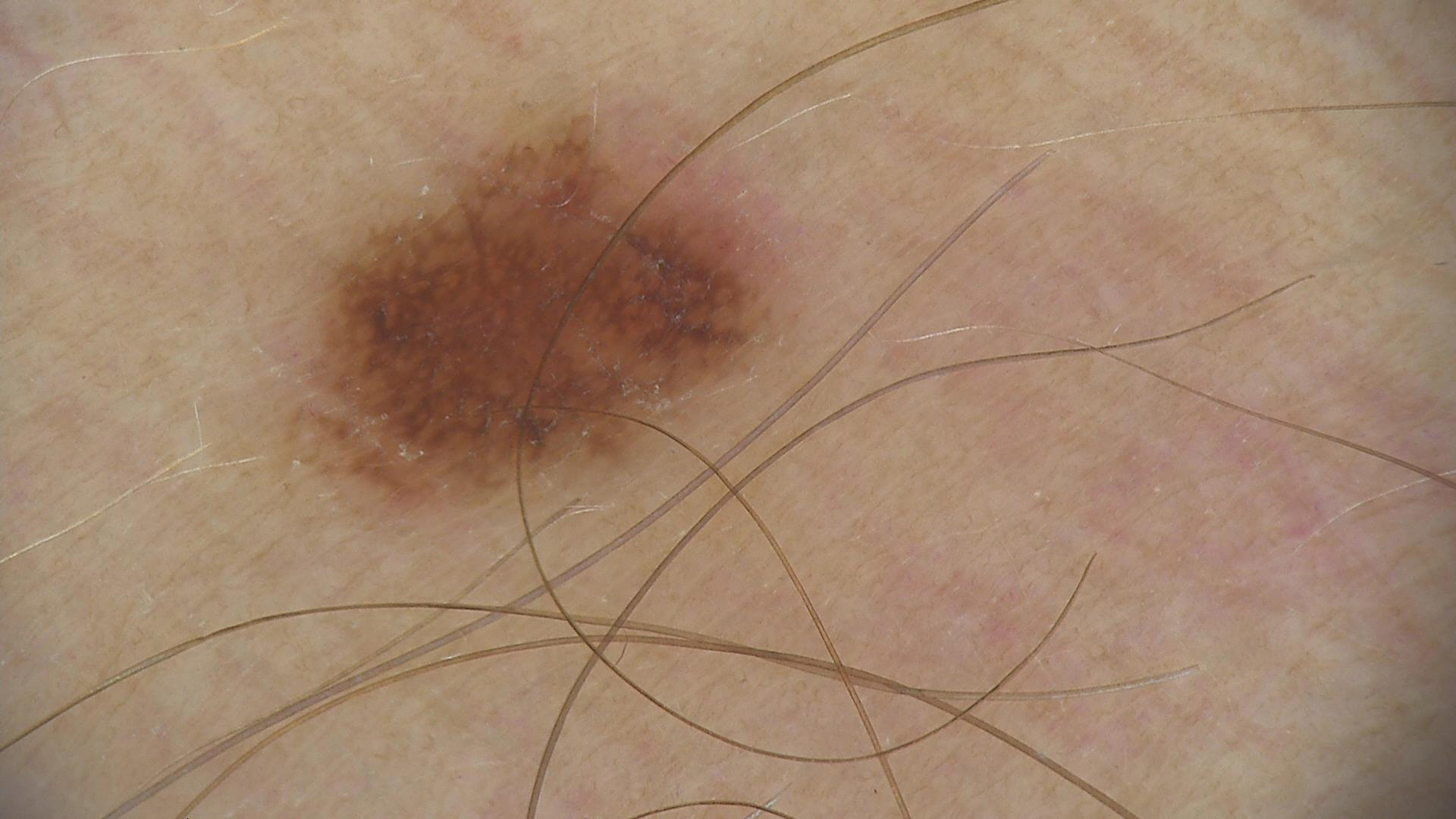The diagnostic label was a dysplastic junctional nevus.